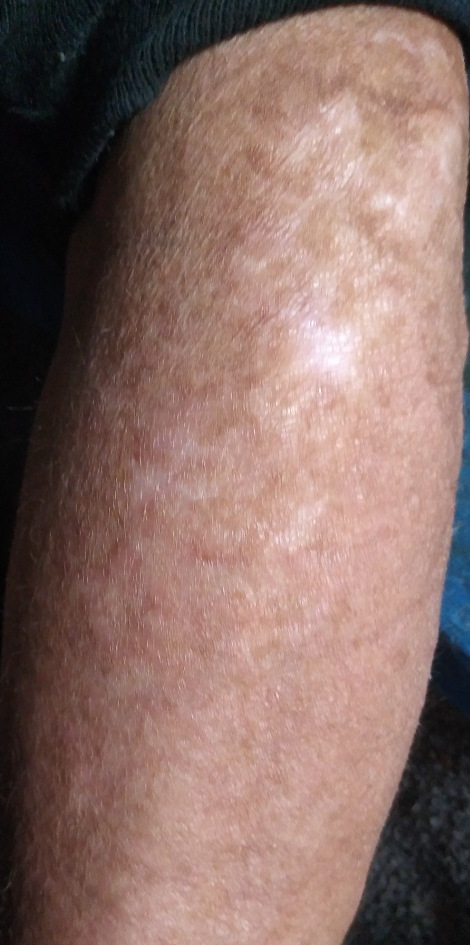The photograph is a close-up of the affected area.